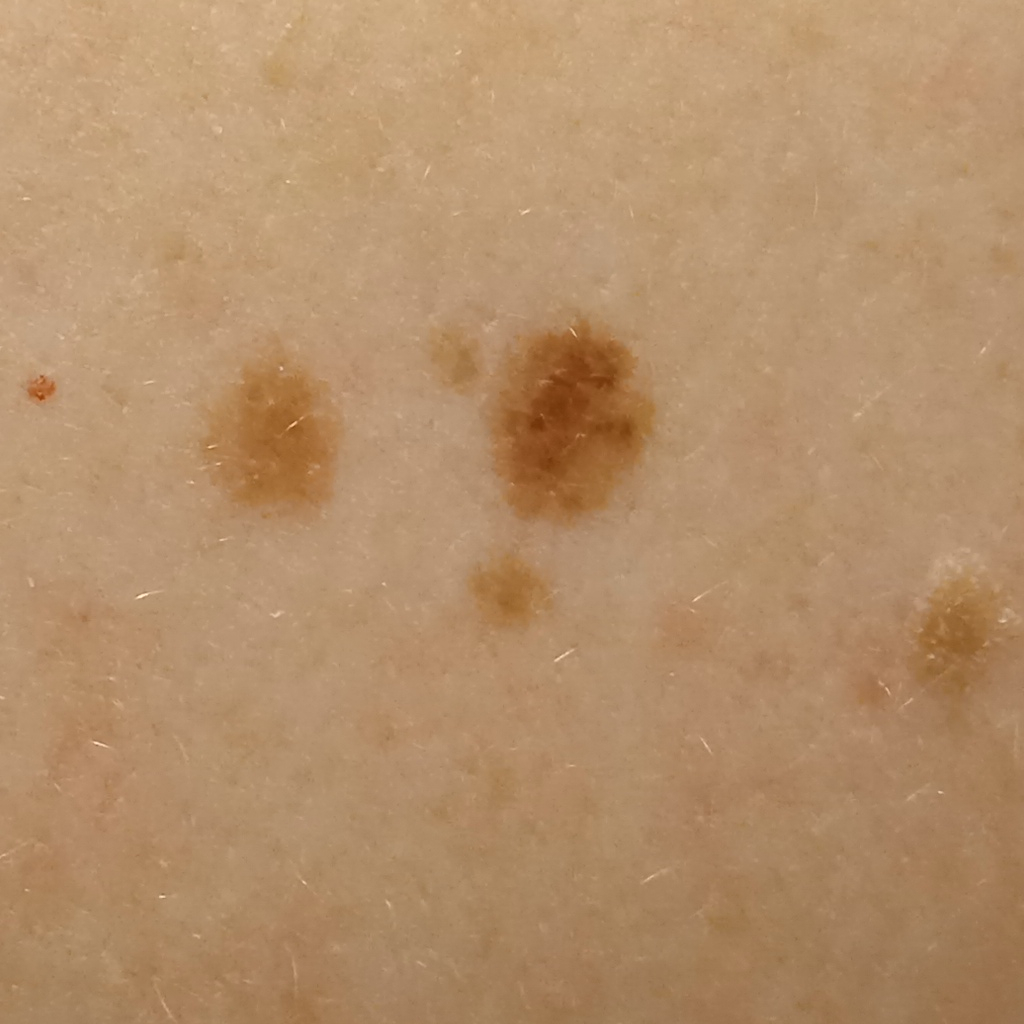diagnosis: atypical (dysplastic) nevus — dermatologist consensus